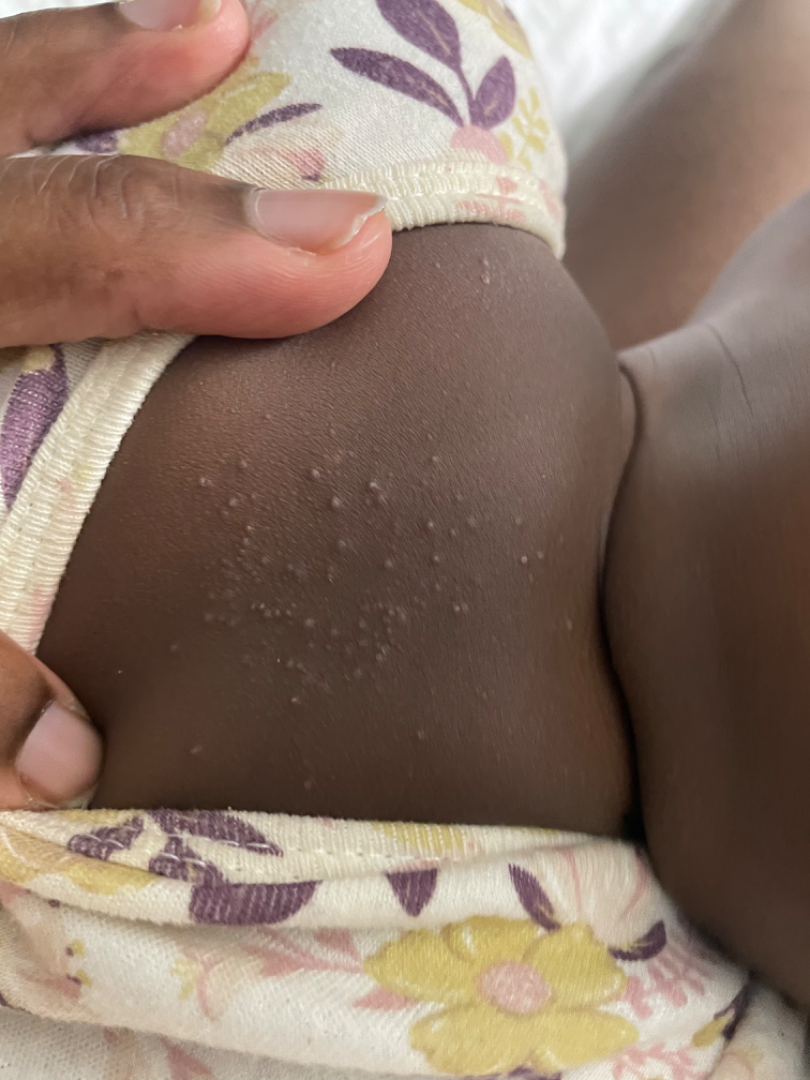On teledermatology review, Eczema (most likely); Miliaria (considered).